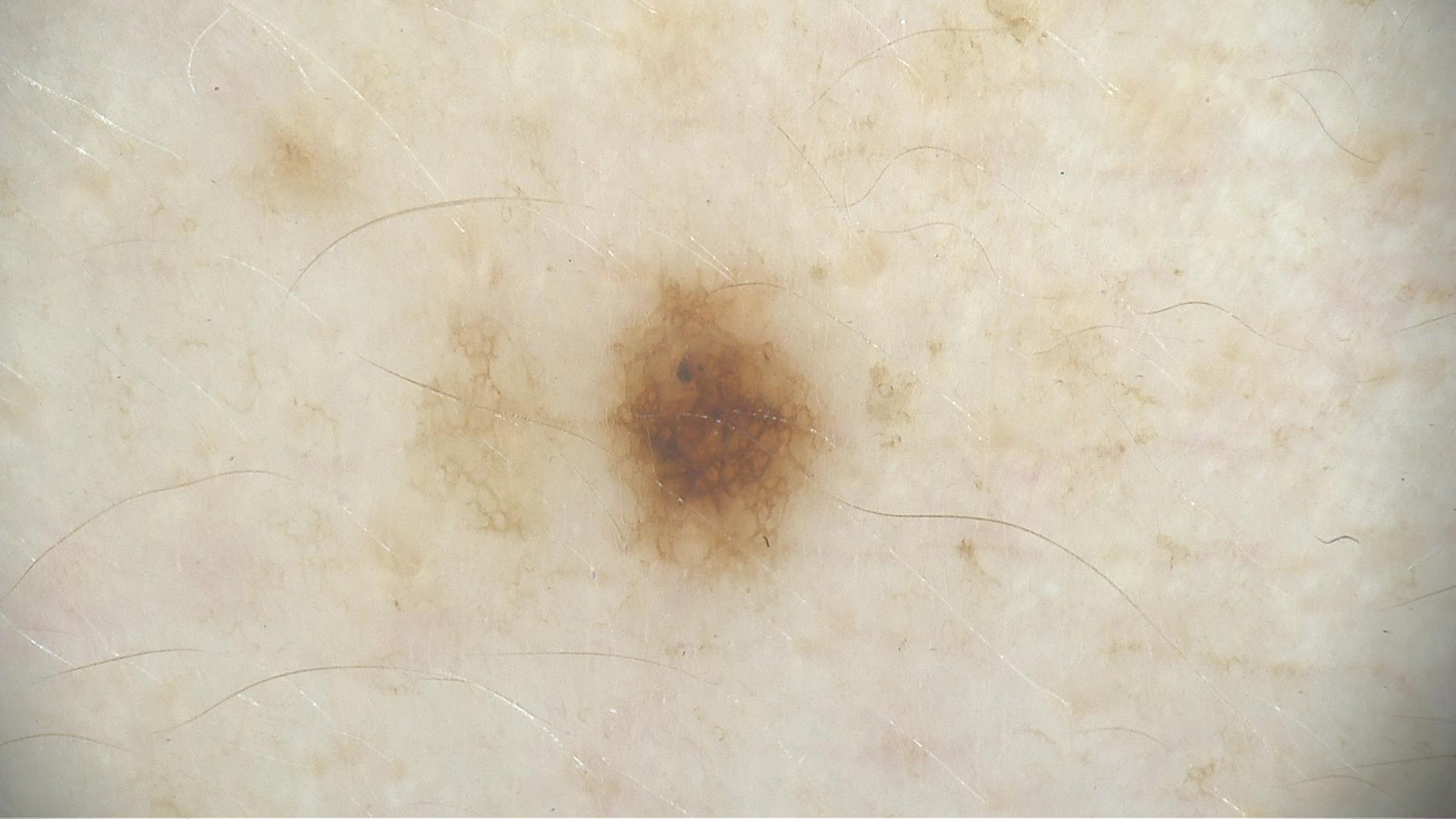Conclusion:
The diagnostic label was a benign lesion — a dysplastic junctional nevus.